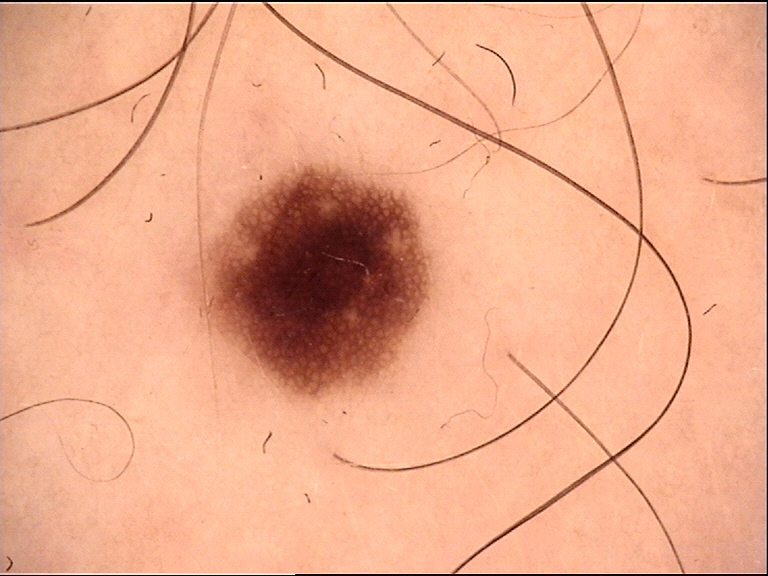label: dysplastic junctional nevus (expert consensus).